Located on the arm. The subject is 18–29, female. A close-up photograph.
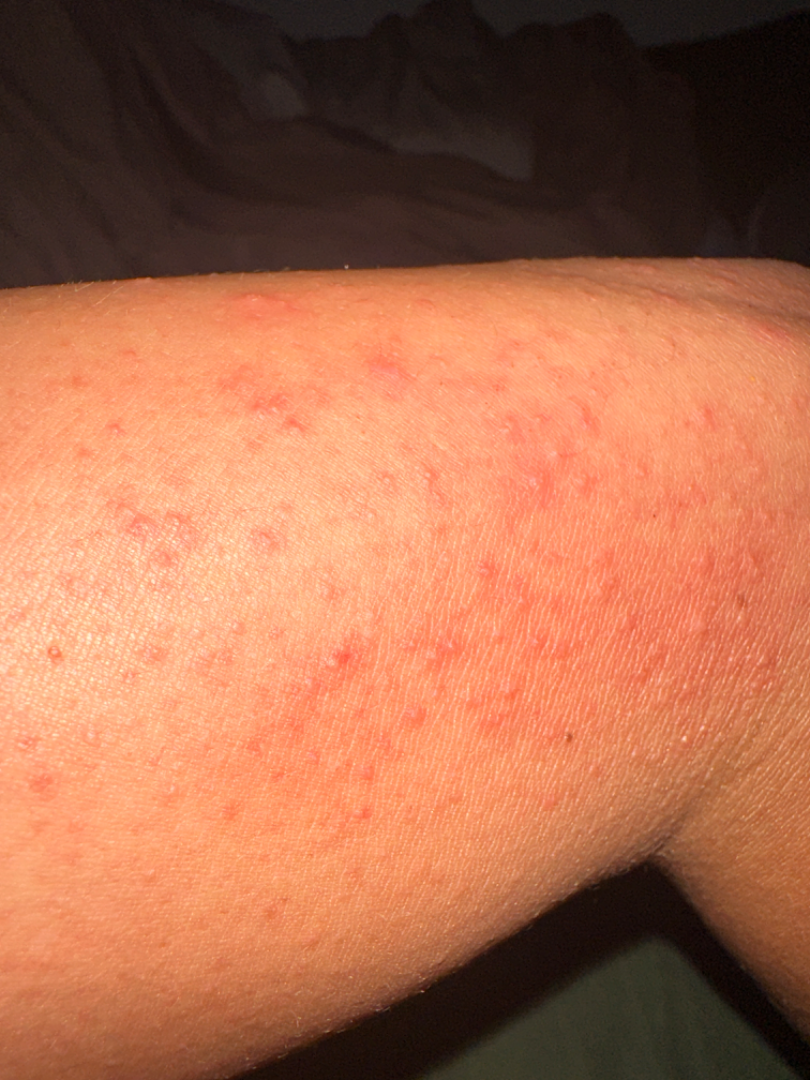systemic_symptoms: none reported
texture:
  - raised or bumpy
  - fluid-filled
symptoms:
  - itching
  - bothersome appearance
duration: one to four weeks
differential:
  leading:
    - Acute dermatitis, NOS